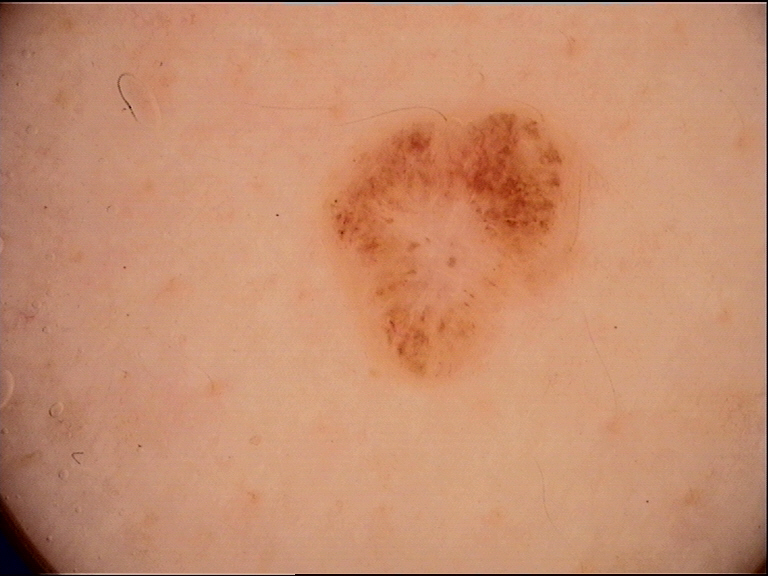Summary: A skin lesion imaged with a dermatoscope. Impression: Classified as a dysplastic compound nevus.